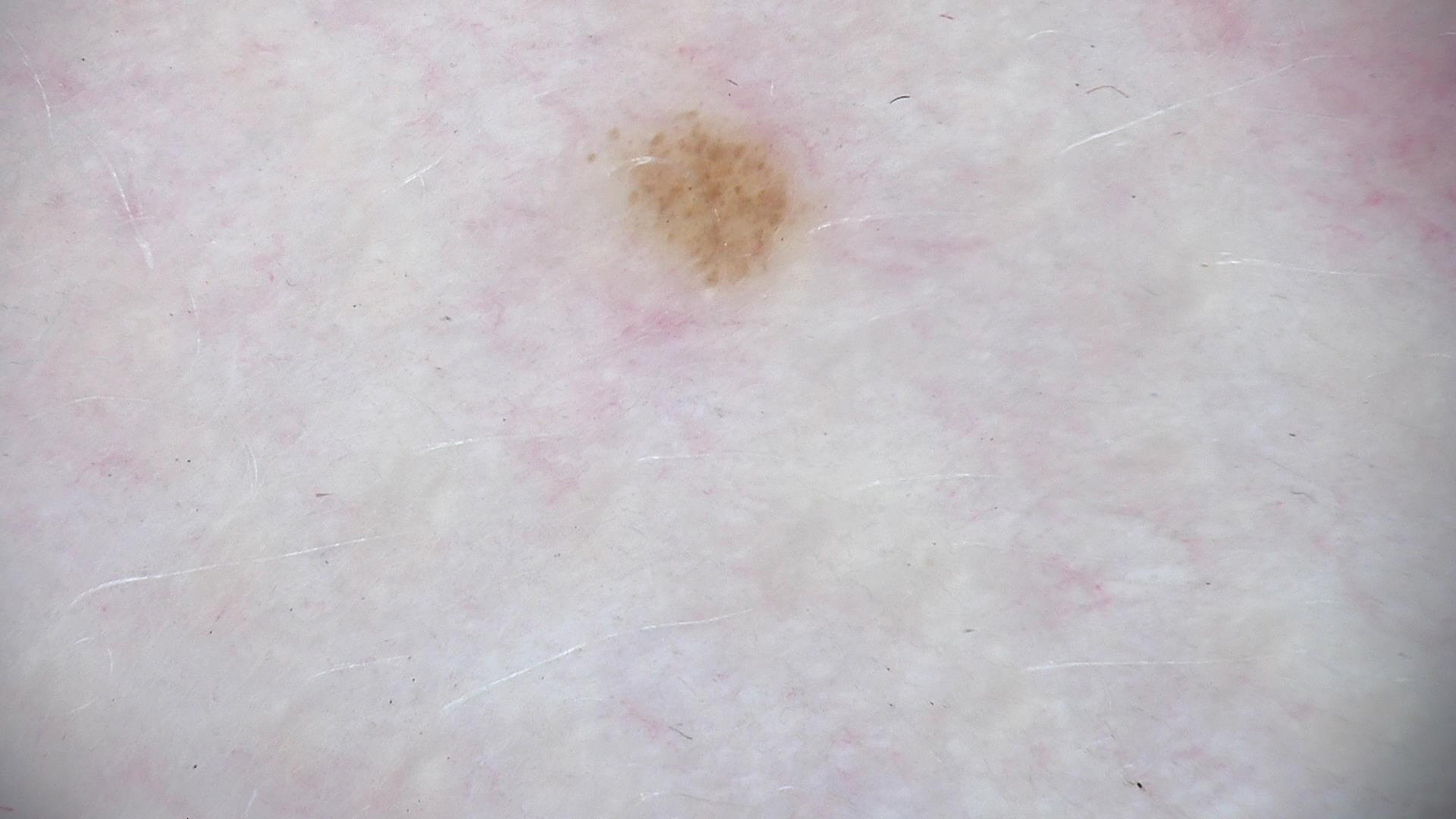label — compound nevus (expert consensus)